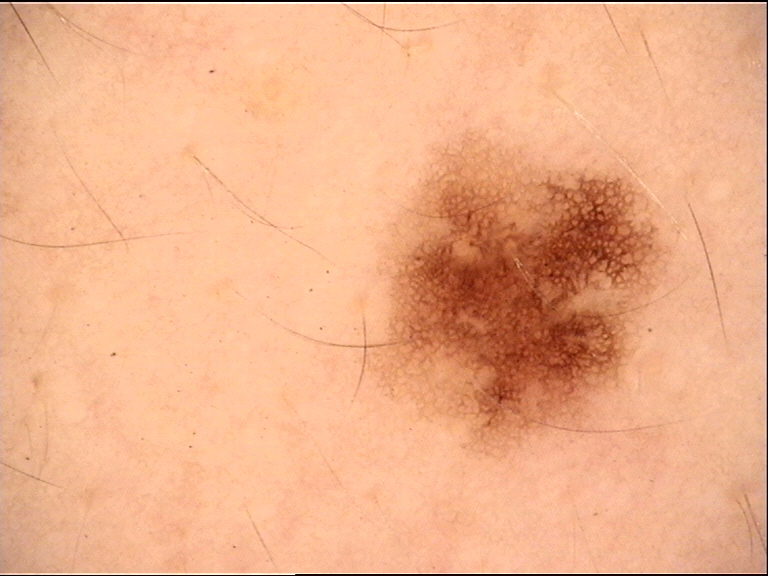image = dermoscopy; category = banal; assessment = junctional nevus (expert consensus).